The photograph is a close-up of the affected area.
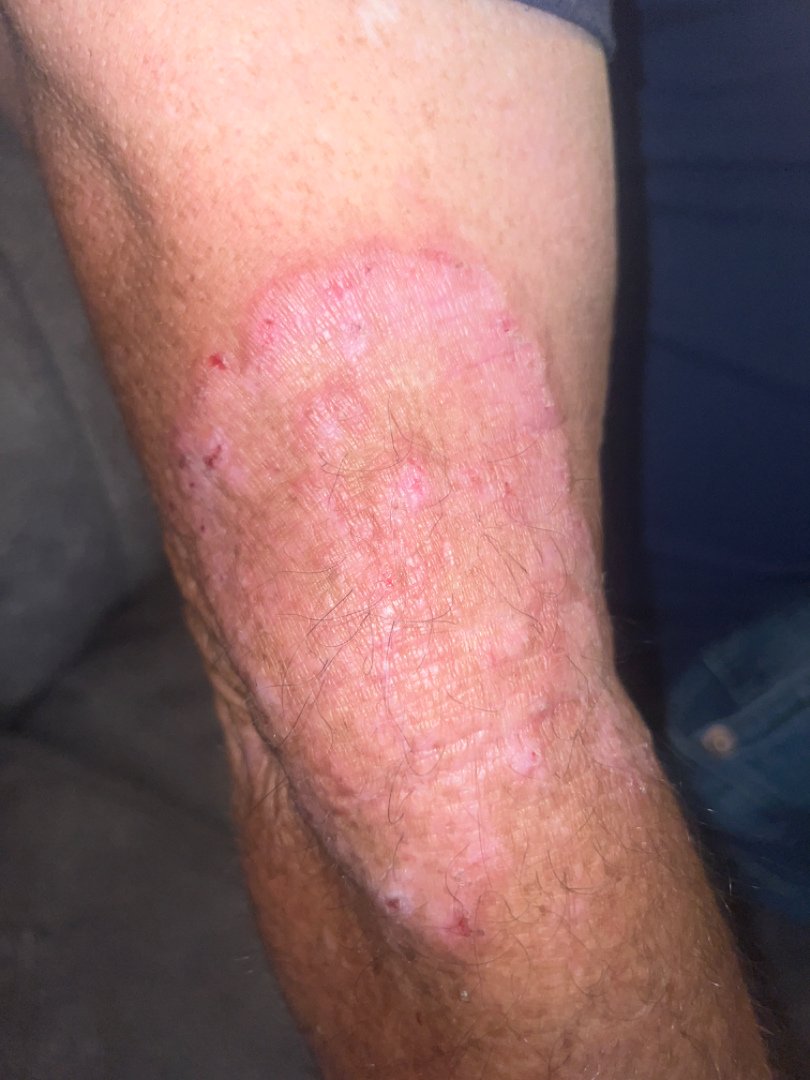Patient information: Skin tone: lay reviewers estimated Monk Skin Tone 5 (US pool) or 3 (India pool). Review: Most consistent with Tinea; also raised was Granuloma annulare; also consider Psoriasis.